A dermoscopic image of a skin lesion.
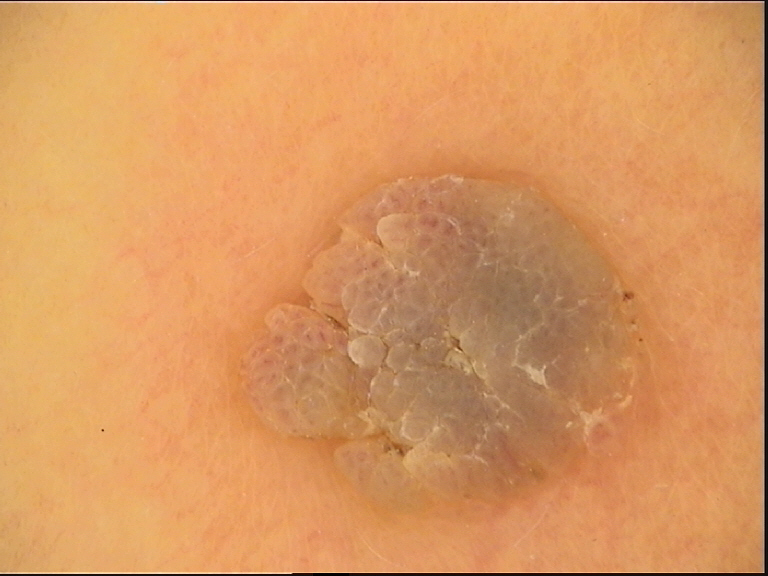diagnostic label = seborrheic keratosis (expert consensus)